The subject is a male aged 18–29, close-up view — 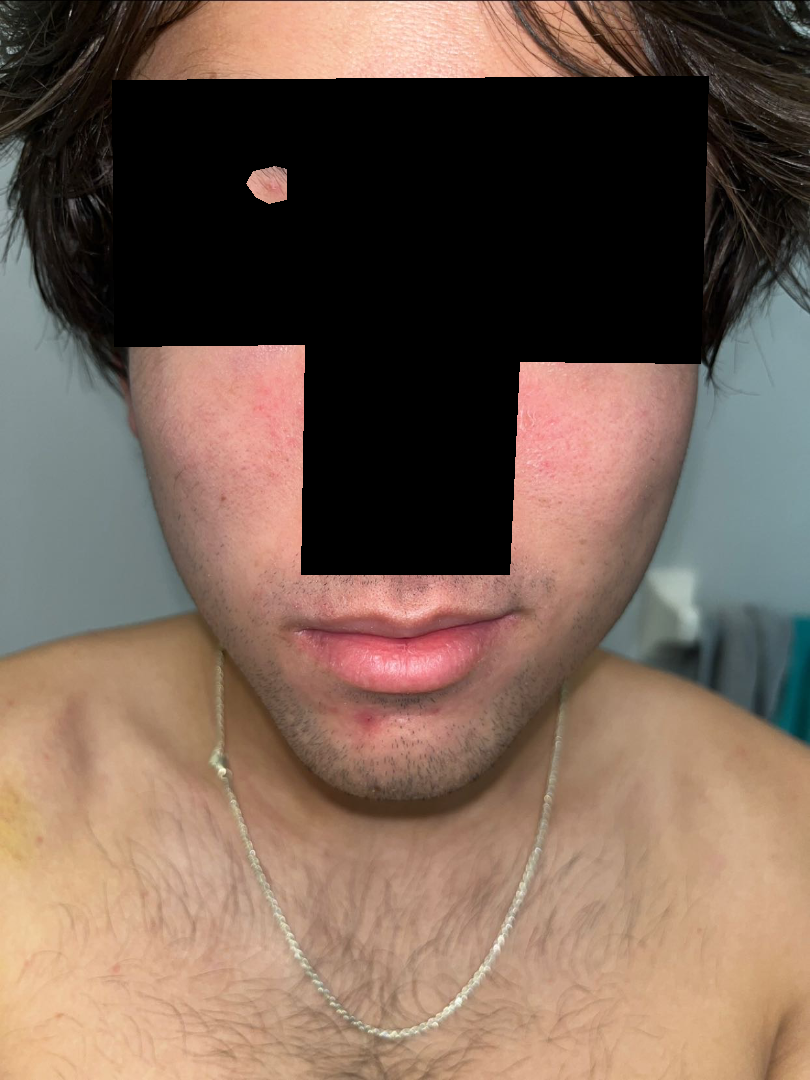{"differential": {"leading": ["Acne"], "considered": ["Folliculitis"]}}